Present for one to three months; texture is reported as rough or flaky; located on the back of the torso, arm and leg; the photo was captured at a distance; reported lesion symptoms include bleeding, bothersome appearance, itching and enlargement; the contributor is a female aged 40–49:
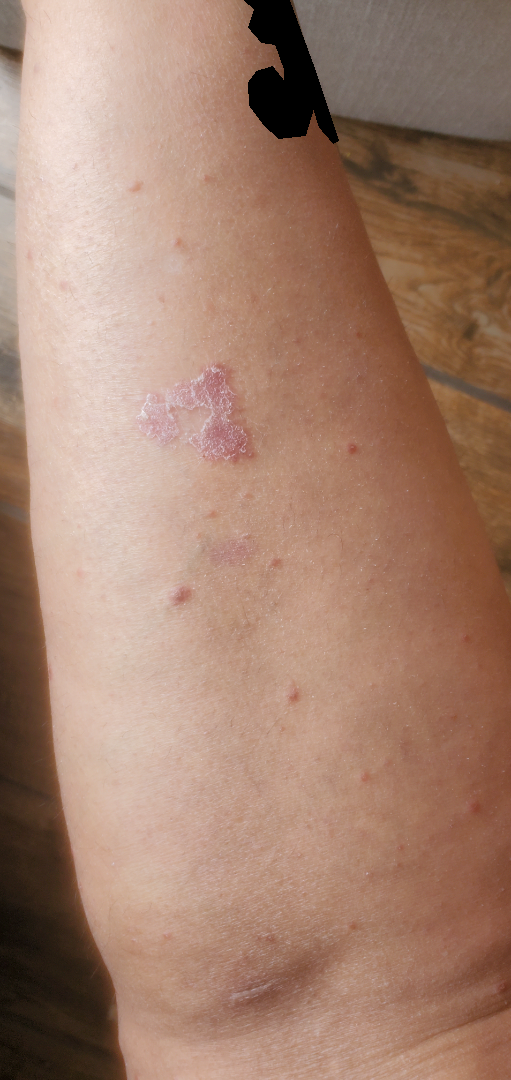Case summary:
* assessment — the favored diagnosis is Psoriasis; the differential also includes Lichen planus/lichenoid eruption; a more distant consideration is Porokeratosis